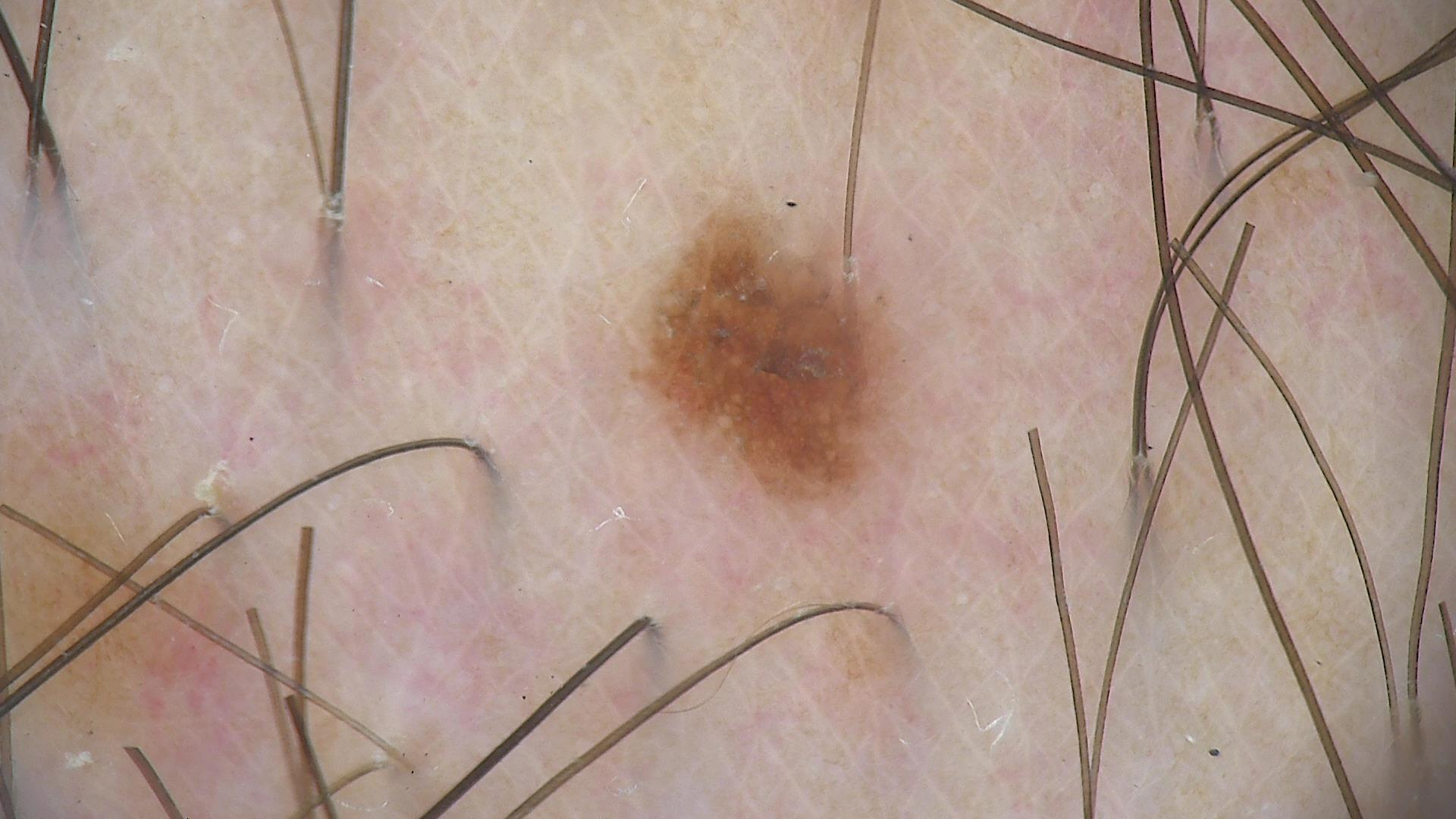image: dermoscopy, diagnostic label: dysplastic junctional nevus (expert consensus).